The contributor reports the lesion is rough or flaky · lay graders estimated MST 3 or 4 (two reviewer pools) · the patient considered this a rash · male patient, age 18–29 · the photo was captured at an angle · the patient reported no systemic symptoms · the lesion involves the head or neck: 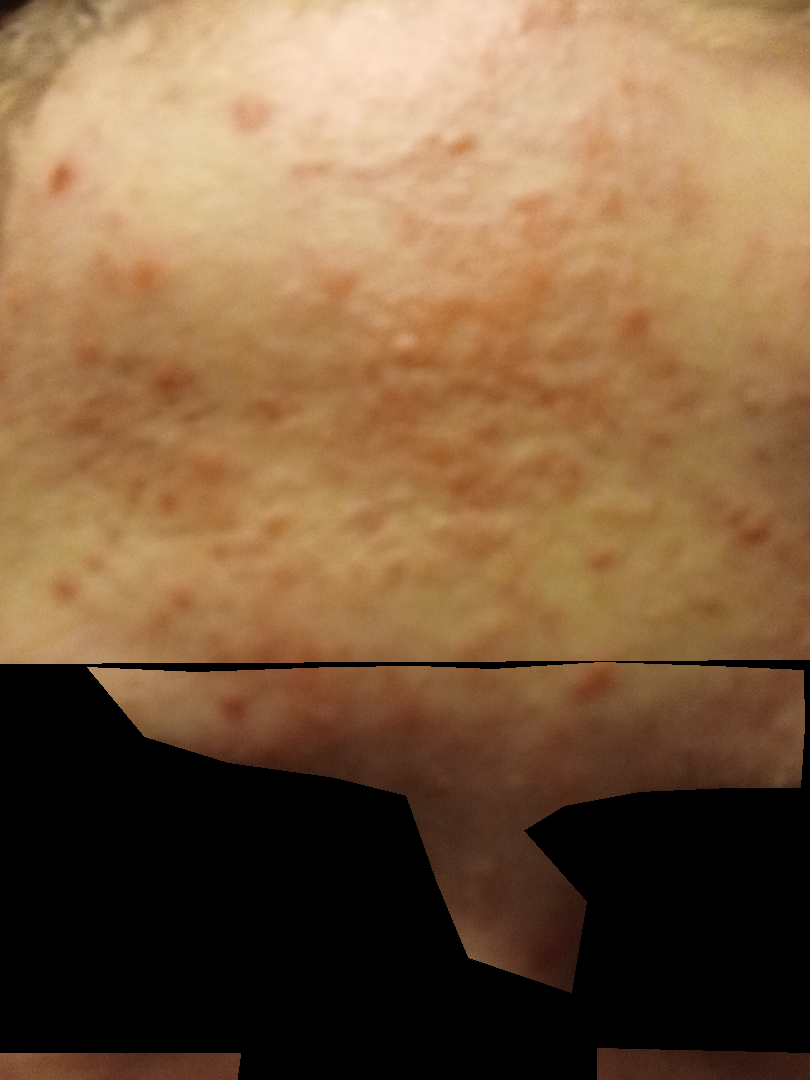Review: On dermatologist assessment of the image, the leading consideration is Acne; an alternative is Irritant Contact Dermatitis.